The patient reports a personal history of cancer, no prior organ transplant, and no immunosuppression; the patient says their skin reddens with sun exposure; a skin lesion imaged with a dermatoscope; the patient describes having numerous moles; a male subject 73 years old; collected as part of a research study, without a referral diagnosis:
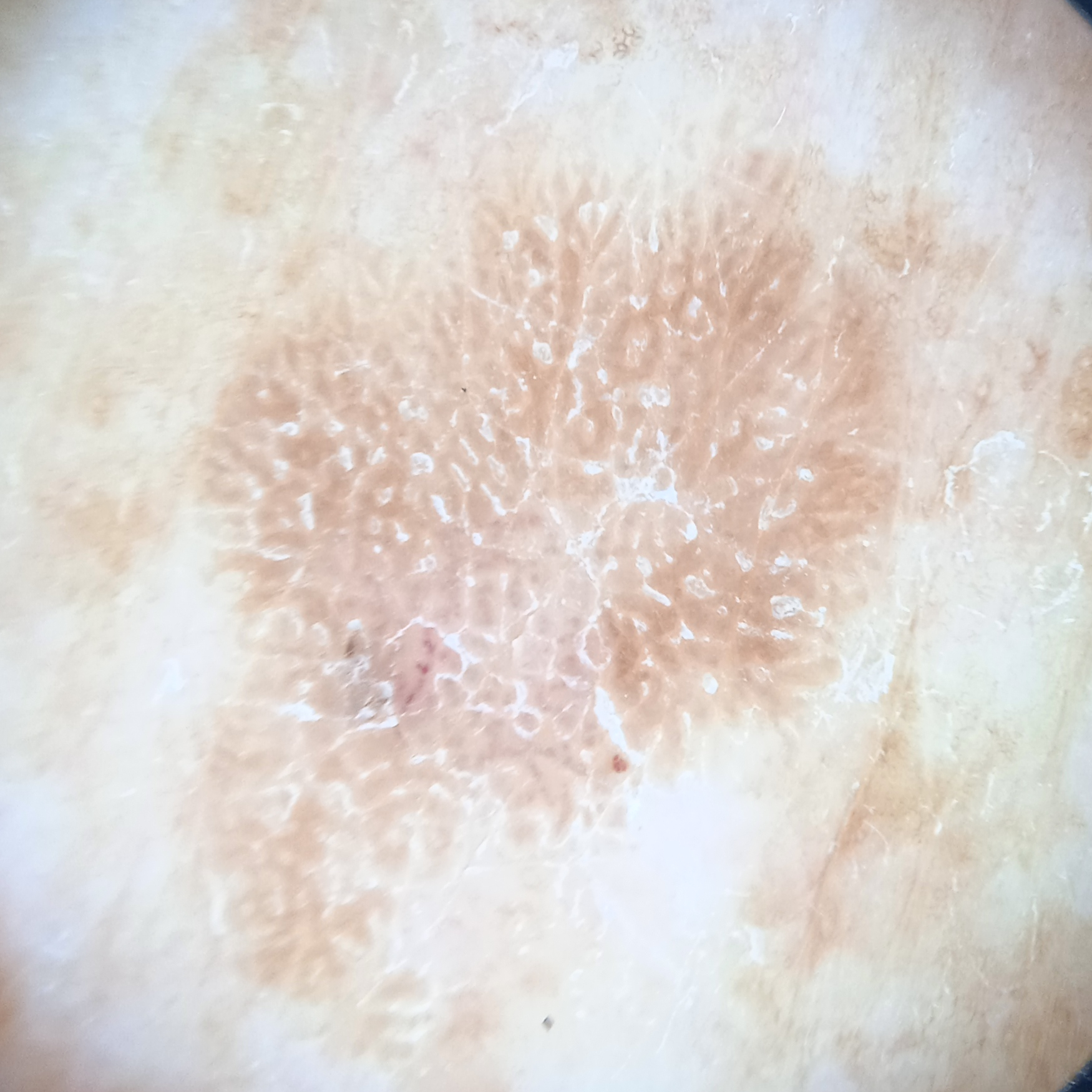Q: Lesion size?
A: 10.7 mm
Q: What was the diagnosis?
A: seborrheic keratosis (dermatologist consensus)